A skin lesion imaged with a dermatoscope; a female patient 72 years of age.
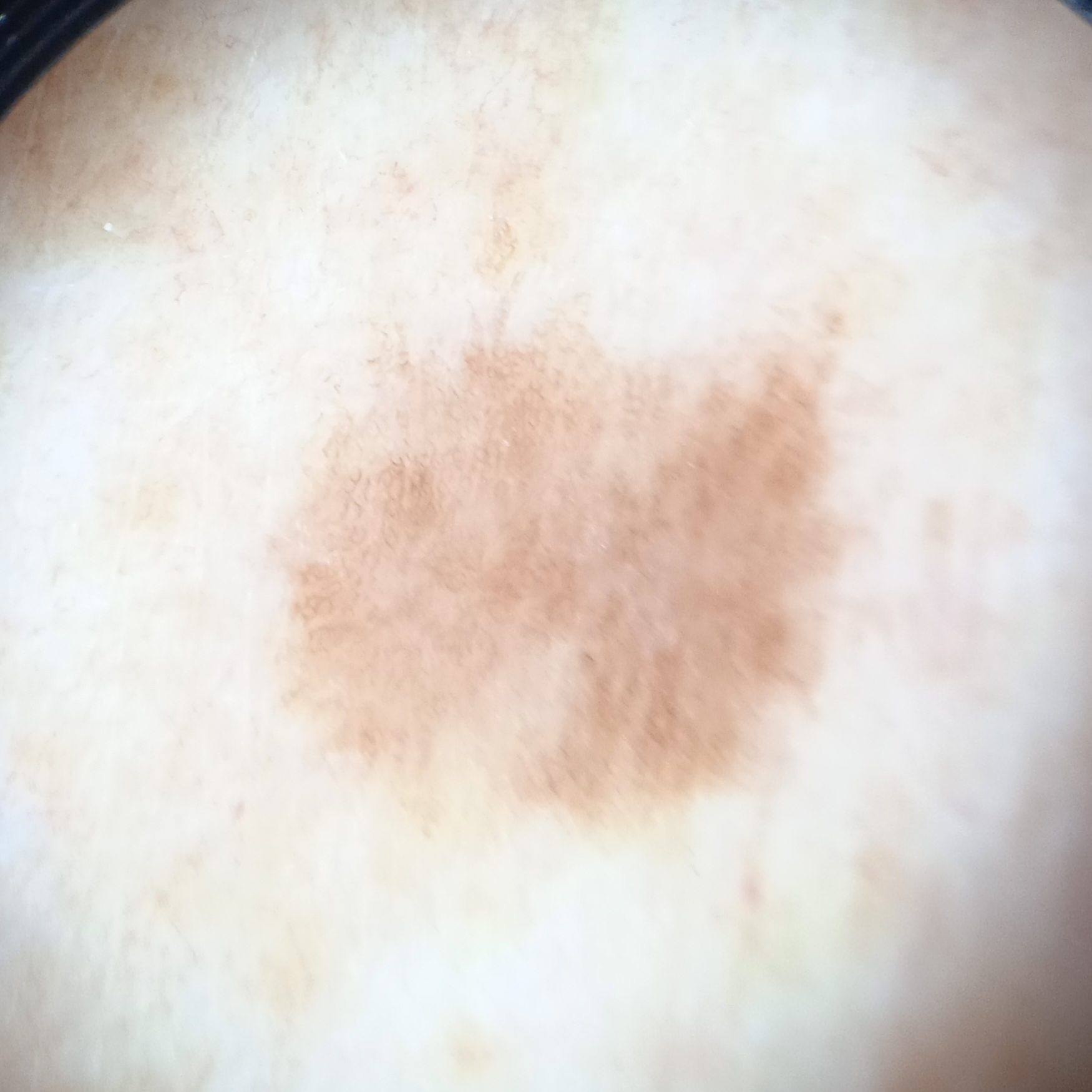The lesion is located on the back.
The lesion measures approximately 7.2 mm.
Reviewed by four dermatologists, the consensus diagnosis was a melanocytic nevus; diagnostic confidence was moderate.